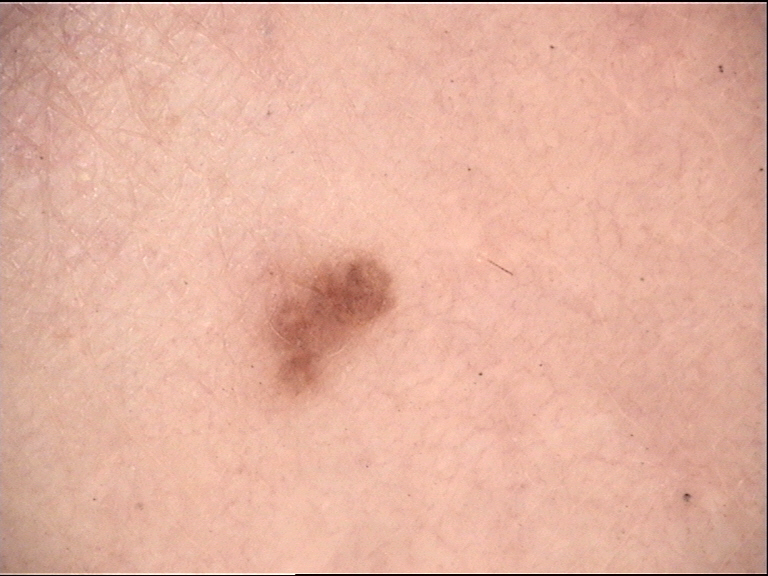Consistent with a benign lesion — a dysplastic junctional nevus.